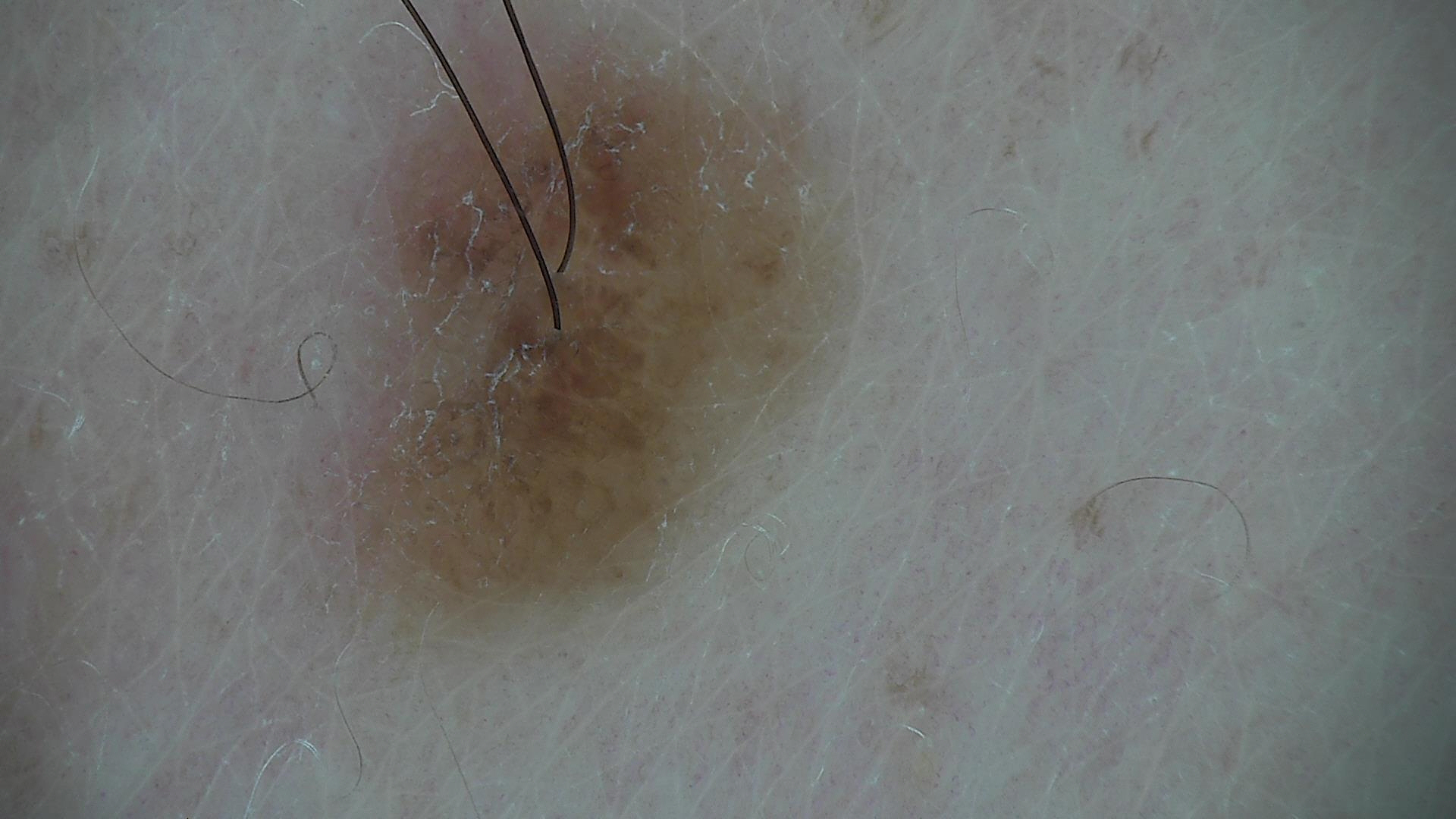<lesion>
<diagnosis>
<name>compound nevus</name>
<code>cb</code>
<malignancy>benign</malignancy>
<super_class>melanocytic</super_class>
<confirmation>expert consensus</confirmation>
</diagnosis>
</lesion>